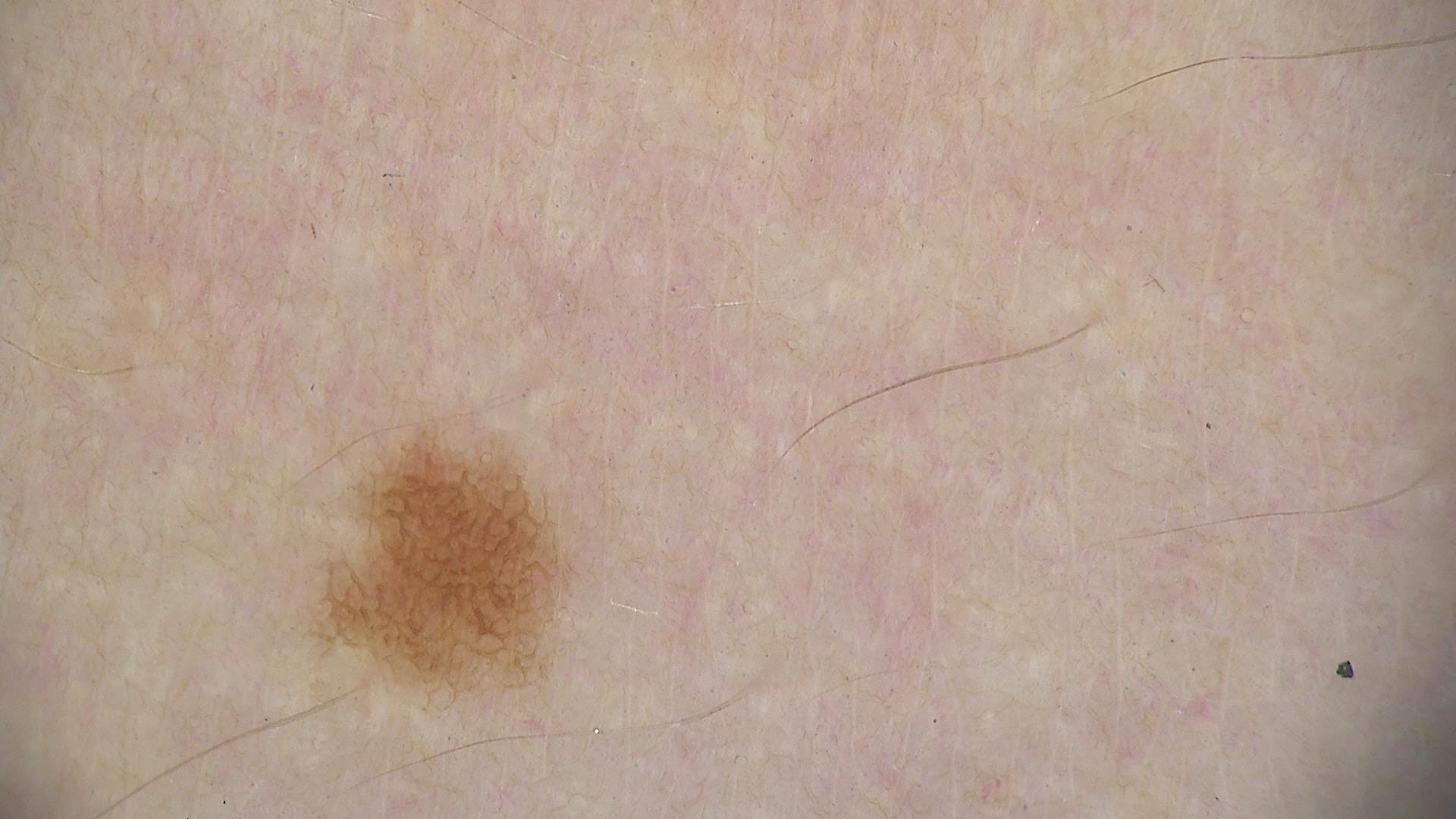image type — dermoscopy
assessment — junctional nevus (expert consensus)